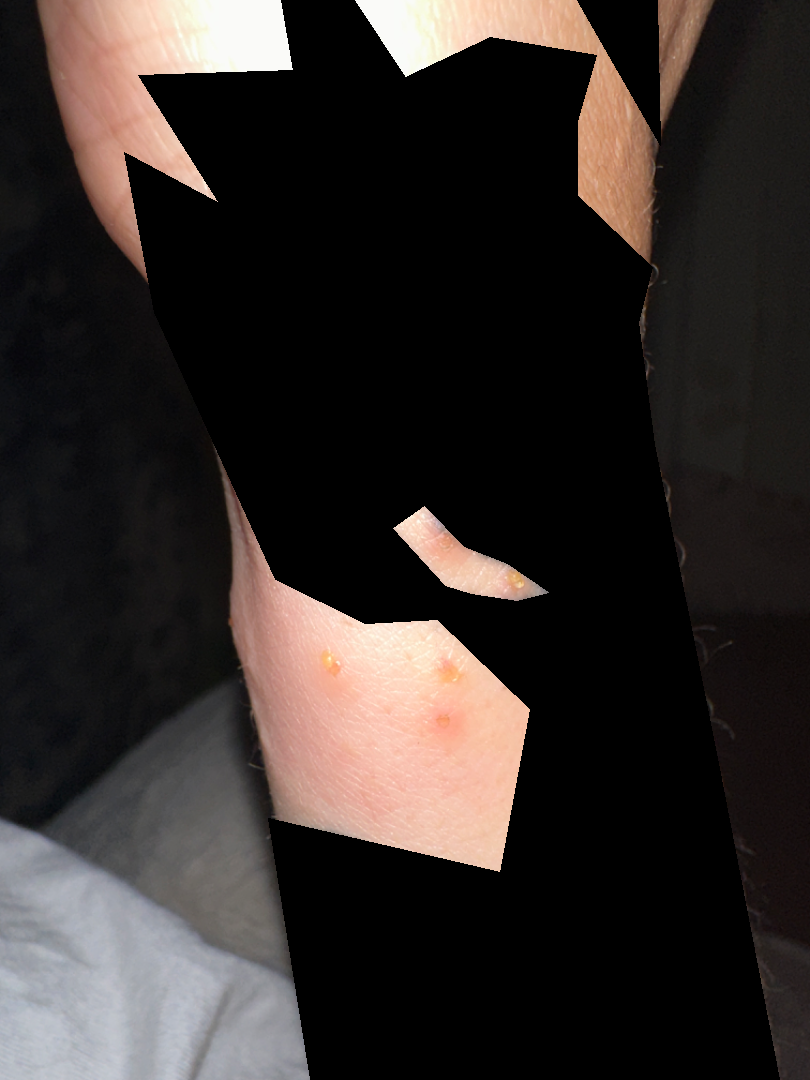diagnostic considerations: Insect Bite (weight 0.22); Impetigo (weight 0.21); Contact dermatitis (weight 0.16); Herpes Simplex (weight 0.16); Acute dermatitis, NOS (weight 0.16); Allergic Contact Dermatitis (weight 0.10).